A clinical photograph of a skin lesion:
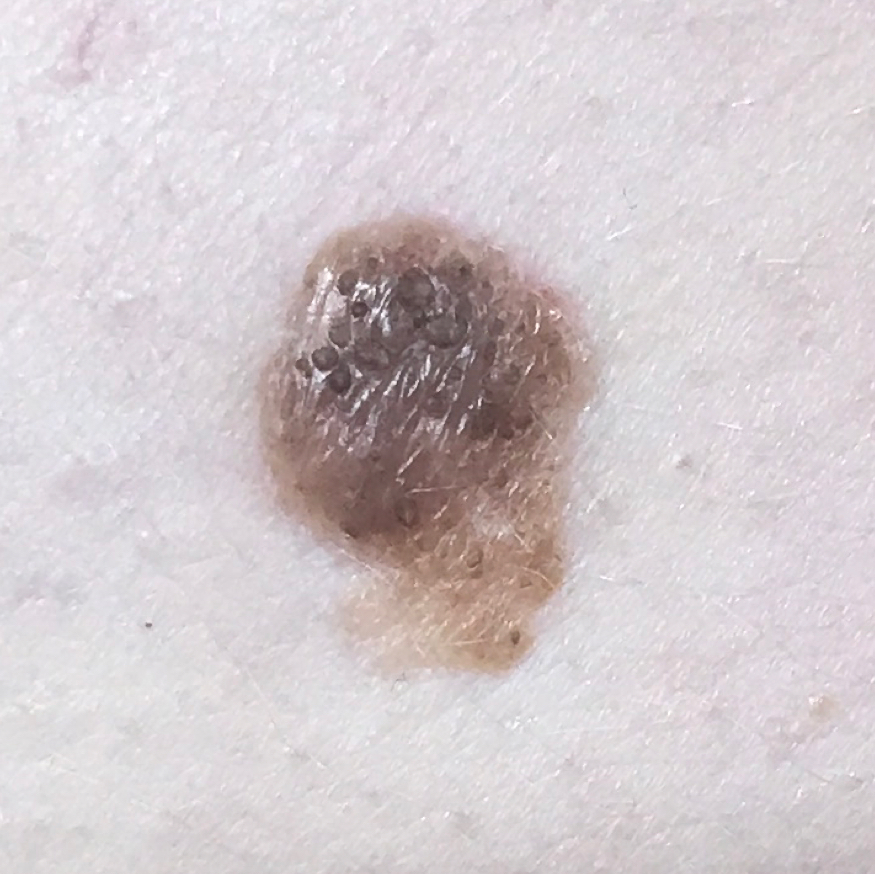location = the chest
reported symptoms = growth, elevation
impression = nevus (clinical consensus)